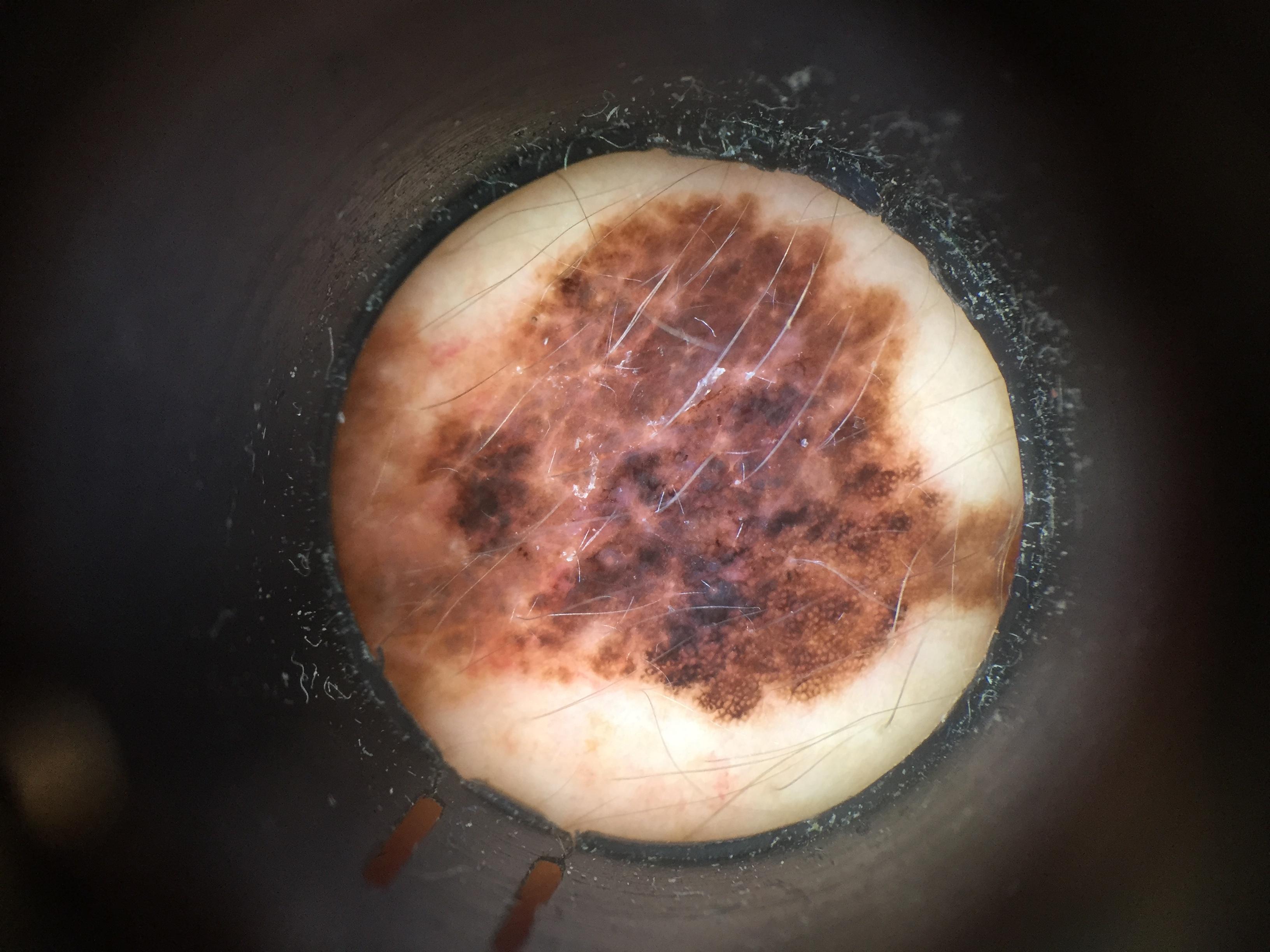Image and clinical context:
Contact-polarized dermoscopy of a skin lesion. A female subject aged 33 to 37. The lesion was found on the trunk.
Diagnosis:
Confirmed on histopathology as a melanoma.